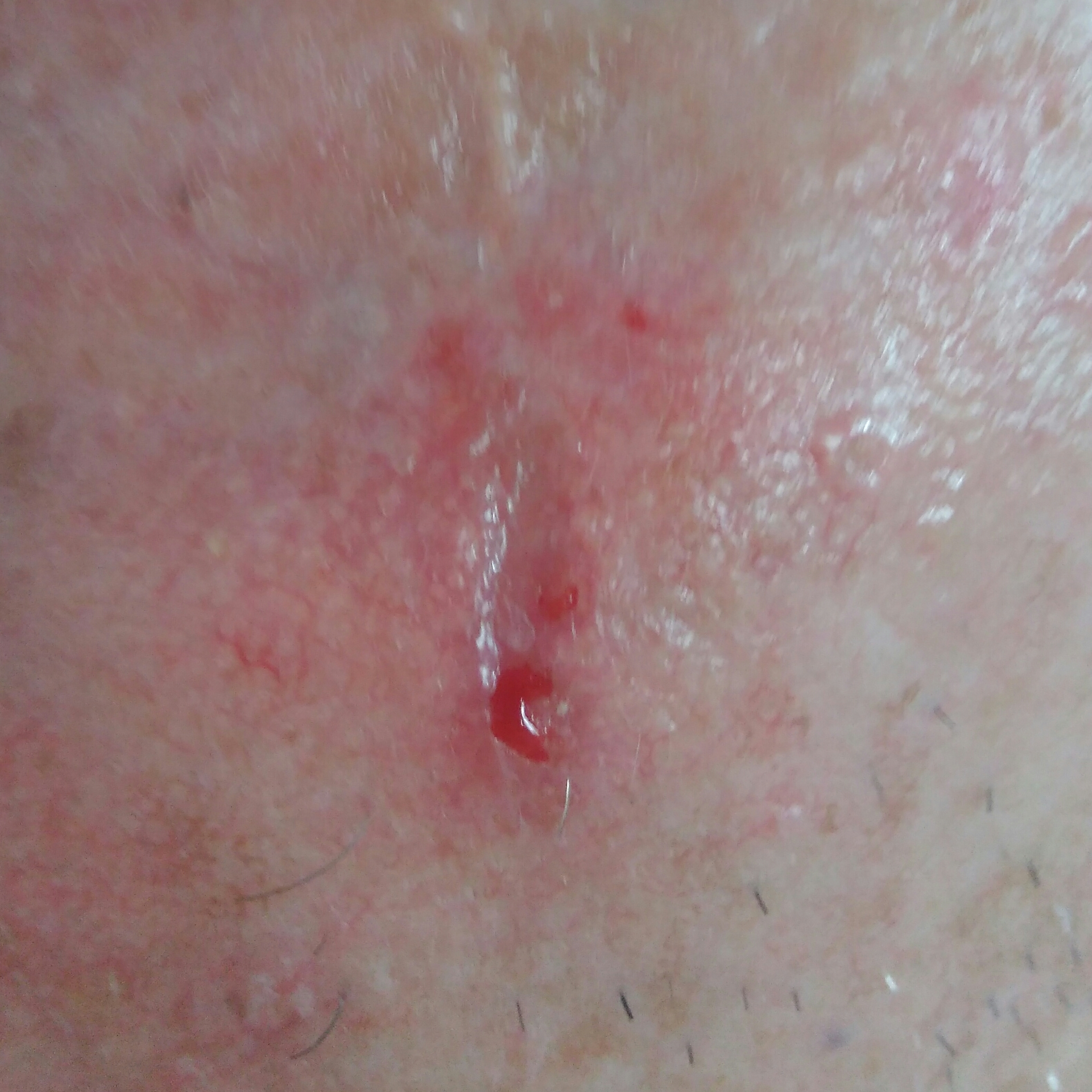skin phototype: III; image type: clinical photograph; subject: male, 70 years of age; risk factors: pesticide exposure, prior skin cancer (patient or family); anatomic site: the face; reported symptoms: elevation, growth, change in appearance; diagnostic label: basal cell carcinoma (biopsy-proven).